The patient is a female aged around 50; dermoscopy of a skin lesion.
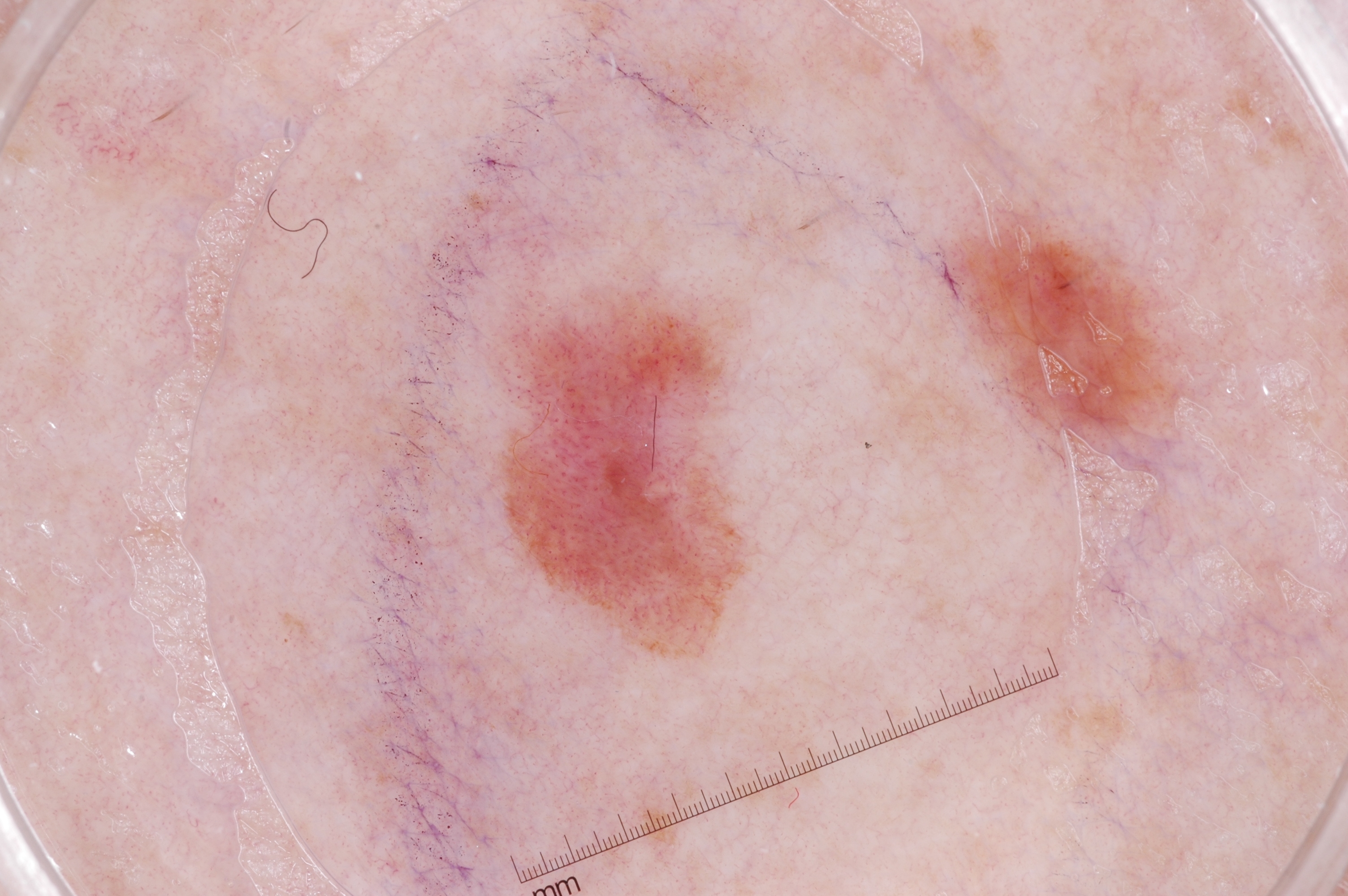Findings:
Dermoscopy demonstrates no milia-like cysts, streaks, negative network, or pigment network. In (x1, y1, x2, y2) order, the lesion's extent is bbox=[482, 264, 761, 667].
Diagnosis:
Histopathologically confirmed as a melanoma.